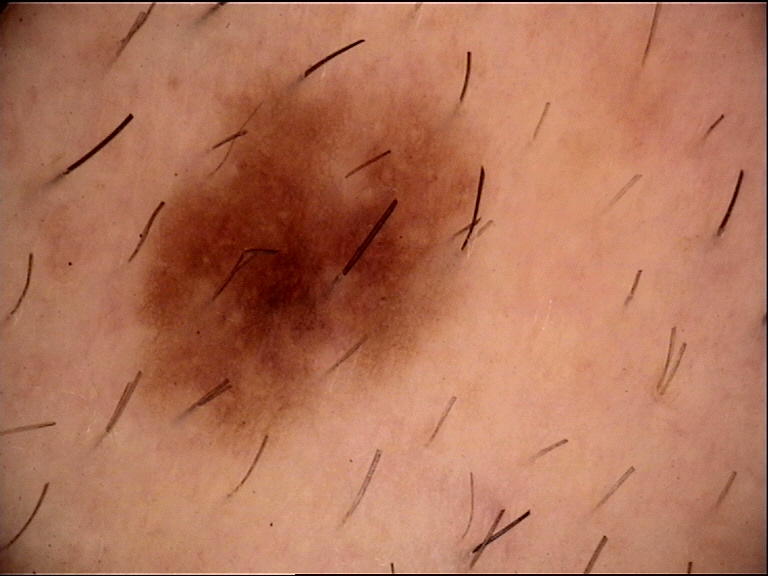Conclusion: The diagnosis was a dysplastic junctional nevus.